The subject is a male aged 73-77. A dermoscopic image of a skin lesion:
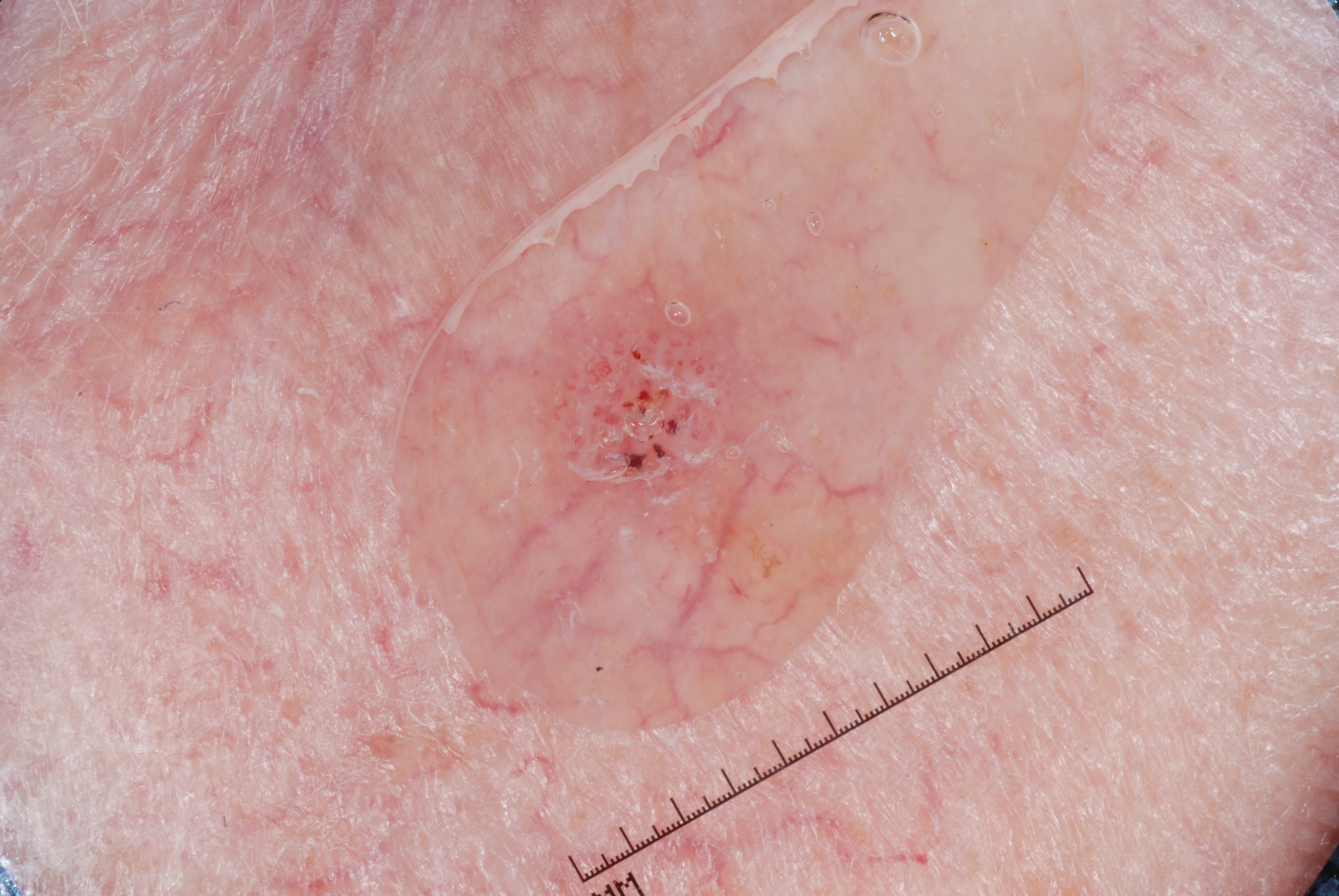On dermoscopy, the lesion shows milia-like cysts; no streaks, negative network, or pigment network. In (x1, y1, x2, y2) order, the lesion is bounded by [509,277,761,519]. The lesion is small relative to the field of view. Diagnosed as a seborrheic keratosis, a non-melanocytic (keratinocytic) lesion.